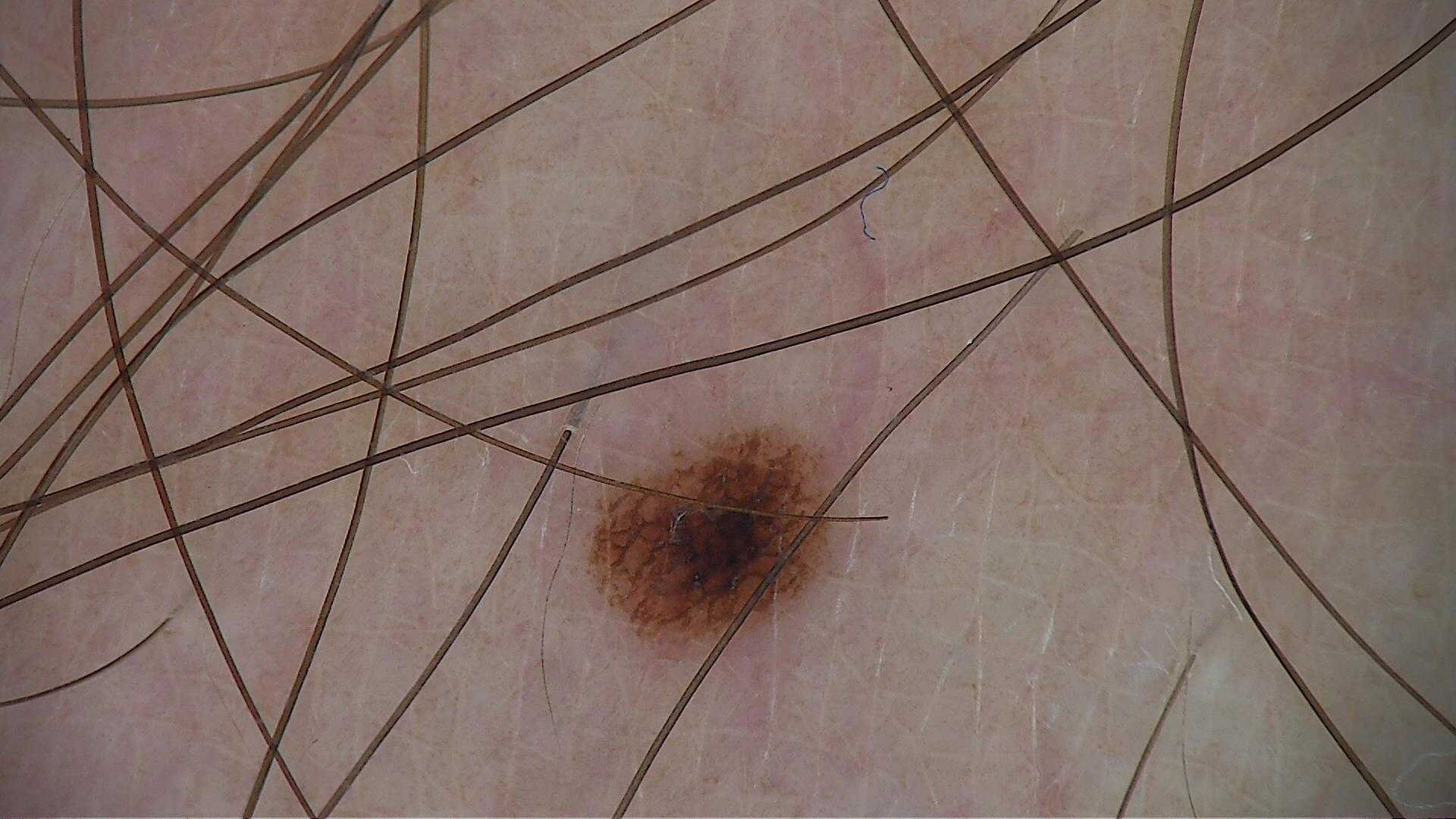The diagnostic label was a junctional nevus.